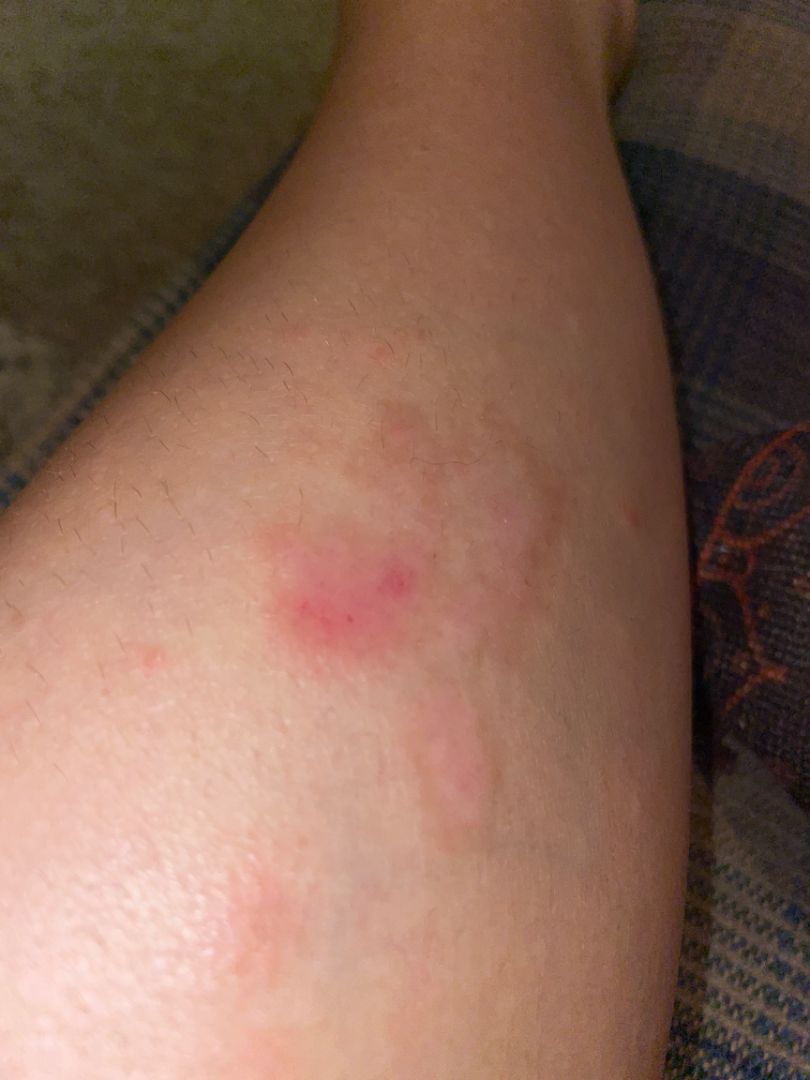Q: Any systemic symptoms?
A: mouth sores and fatigue
Q: Age and sex?
A: female, age 18–29
Q: What is the framing?
A: at an angle
Q: When did this start?
A: three to twelve months
Q: Patient's own categorization?
A: a rash
Q: Texture?
A: rough or flaky
Q: Reported symptoms?
A: itching, bothersome appearance and enlargement
Q: What is the affected area?
A: leg
Q: What is the differential diagnosis?
A: the impression was split between Eczema and Lichen Simplex Chronicus; less probable is Lichen planus/lichenoid eruption; less likely is Morphea/Scleroderma